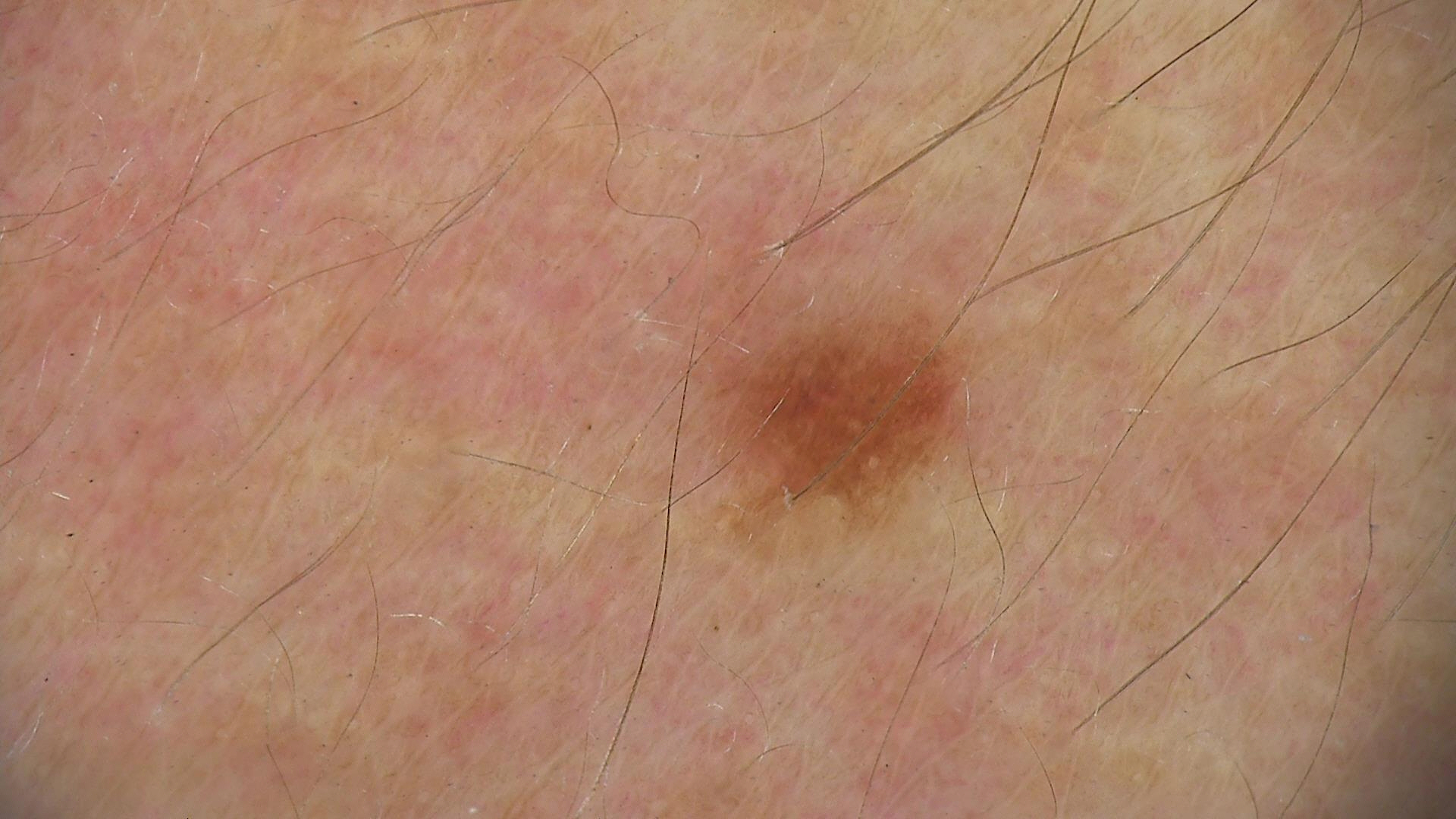Q: What was the diagnostic impression?
A: dysplastic junctional nevus (expert consensus)